Acquired for a research image collection, with no referral diagnosis · the patient describes having a moderate number of moles · the patient reports a personal history of skin cancer and a personal history of cancer · the patient says their skin reddens with sun exposure · a dermoscopy image of a skin lesion · a male subject aged 77:
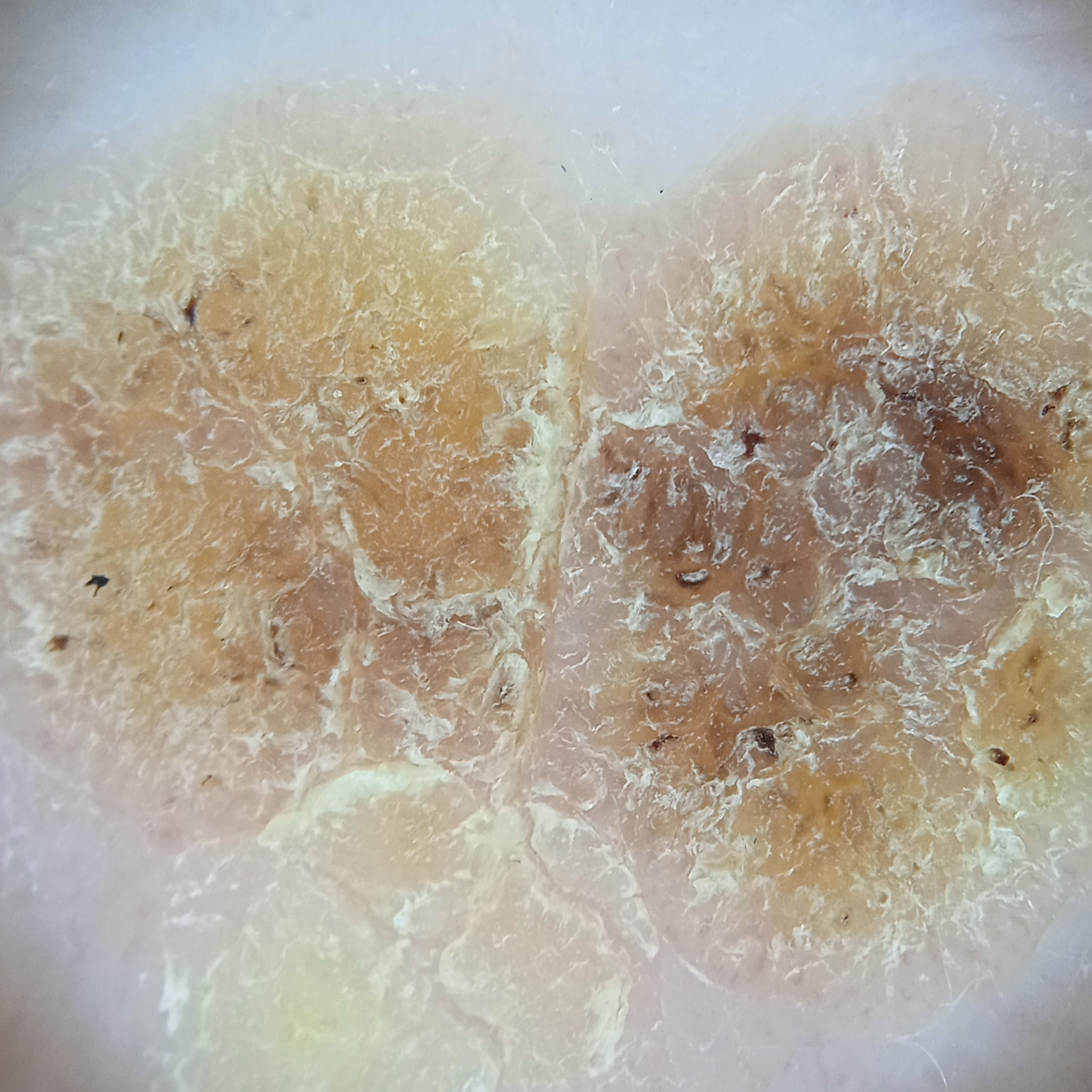Findings:
Measuring roughly 14.2 mm.
Conclusion:
The diagnostic impression was a seborrheic keratosis.